The affected area is the leg, arm, top or side of the foot and back of the hand. A close-up photograph. The contributor is a male aged 40–49.
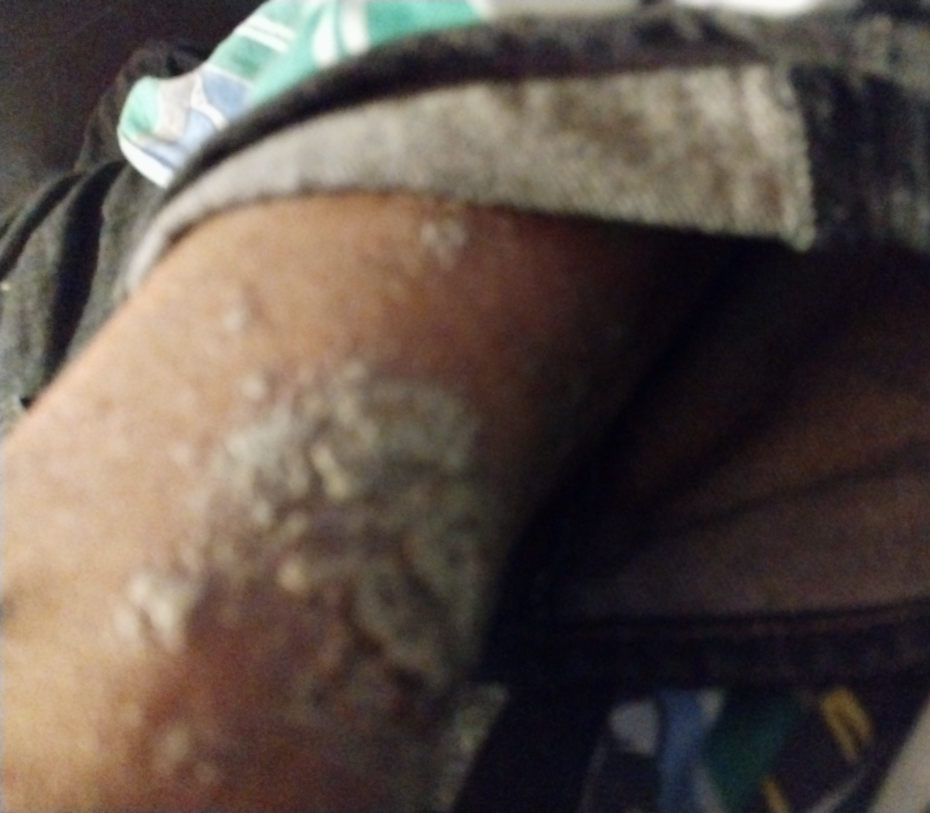Review:
The leading consideration is Psoriasis; also raised was Lichen planus/lichenoid eruption; lower on the differential is Scabies.